Reported duration is less than one week · the patient notes the lesion is raised or bumpy and fluid-filled · the back of the torso, head or neck, top or side of the foot, leg and arm are involved · close-up view · the patient notes pain, burning, enlargement and itching · self-categorized by the patient as a rash: 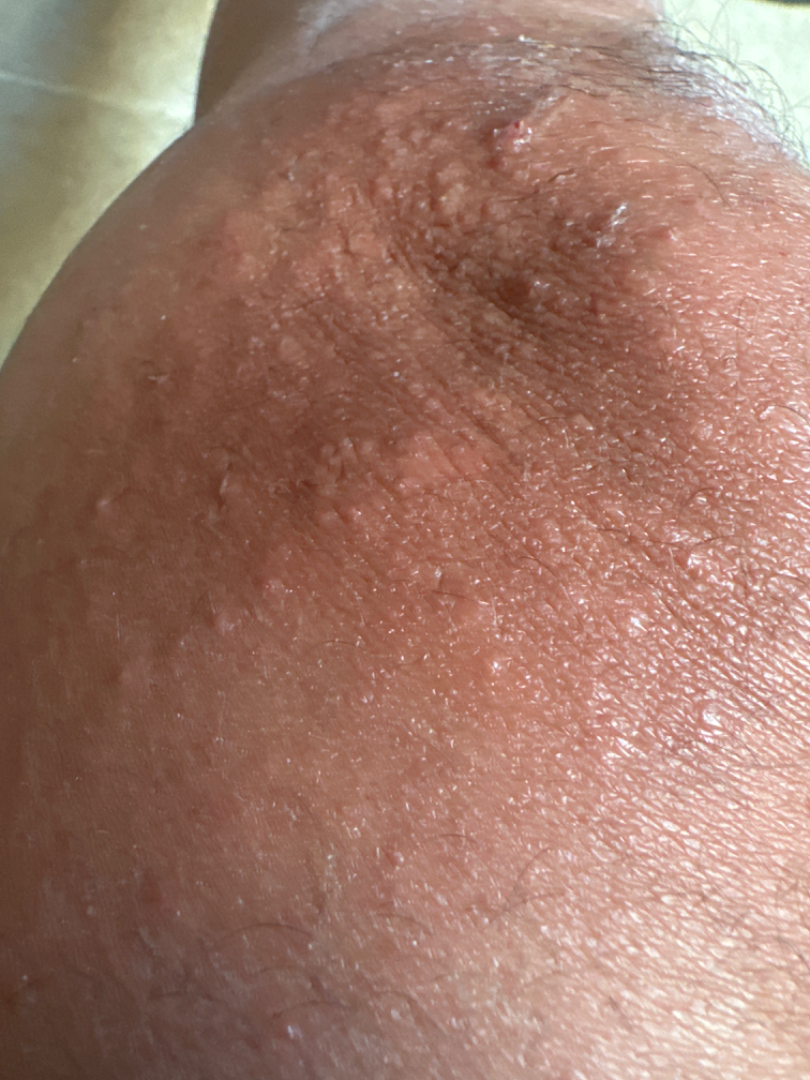On remote dermatologist review: the differential, in no particular order, includes Impetigo, Psoriasis and Allergic Contact Dermatitis.